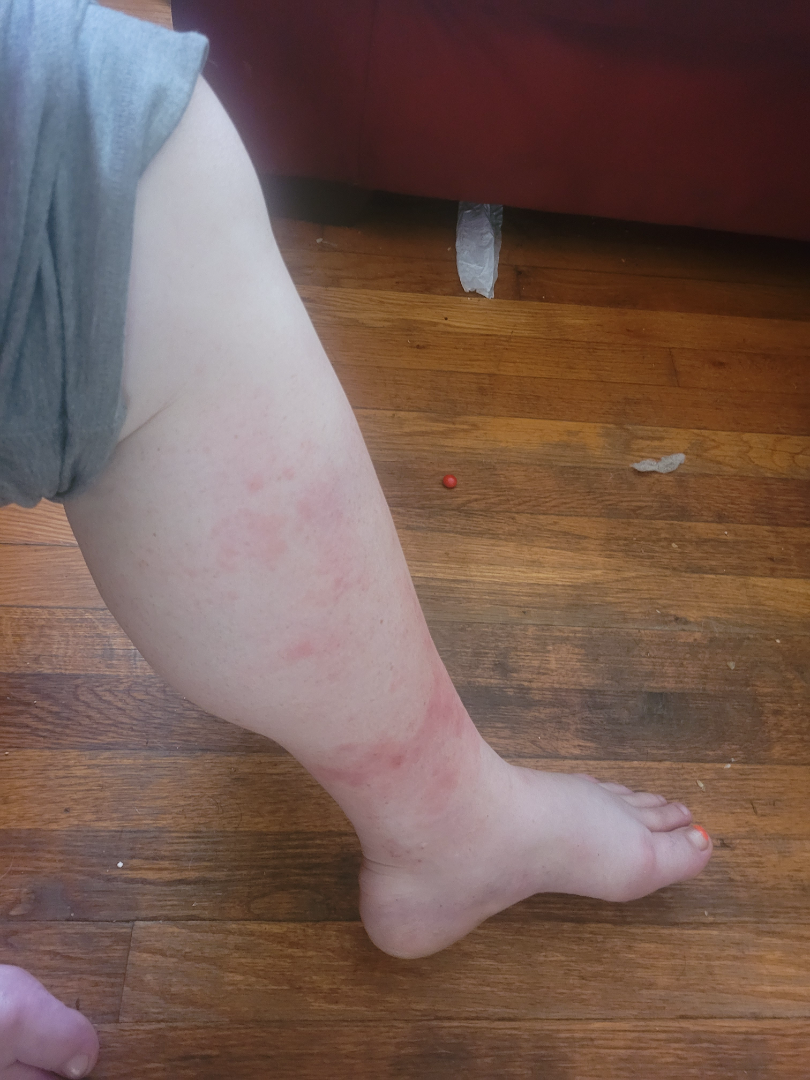Q: When did this start?
A: less than one week
Q: What symptoms does the patient report?
A: enlargement, darkening, bothersome appearance and itching
Q: How does the lesion feel?
A: raised or bumpy
Q: What is the affected area?
A: leg
Q: Patient demographics?
A: female, age 40–49
Q: How does the patient describe it?
A: a rash
Q: What is the framing?
A: at a distance
Q: What is the dermatologist's impression?
A: Stasis Dermatitis, Eczema and Allergic Contact Dermatitis were considered with similar weight